The photograph was taken at a distance · reported lesion symptoms include bothersome appearance and darkening · texture is reported as flat · male patient, age 40–49 · located on the leg · self-categorized by the patient as a rash · reported duration is about one day.
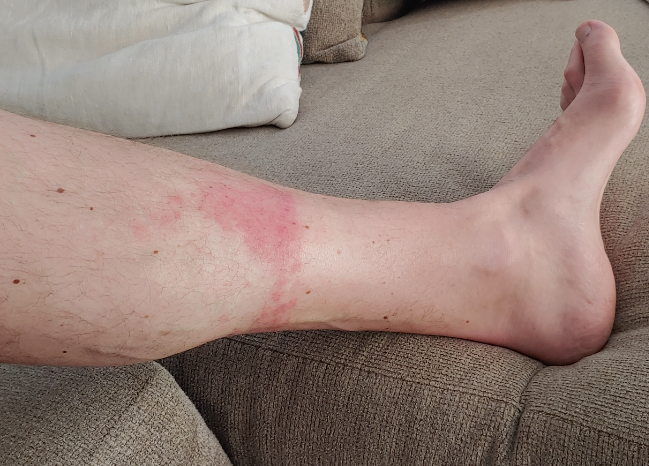{
  "differential": {
    "leading": [
      "Allergic Contact Dermatitis"
    ],
    "considered": [
      "Irritant Contact Dermatitis"
    ]
  }
}